No constitutional symptoms were reported · self-categorized by the patient as skin that appeared healthy to them · the lesion involves the back of the hand, arm and leg · close-up view · the patient is a male aged 18–29 · the lesion is described as rough or flaky and raised or bumpy · symptoms reported: itching · the patient reports the condition has been present for about one day: 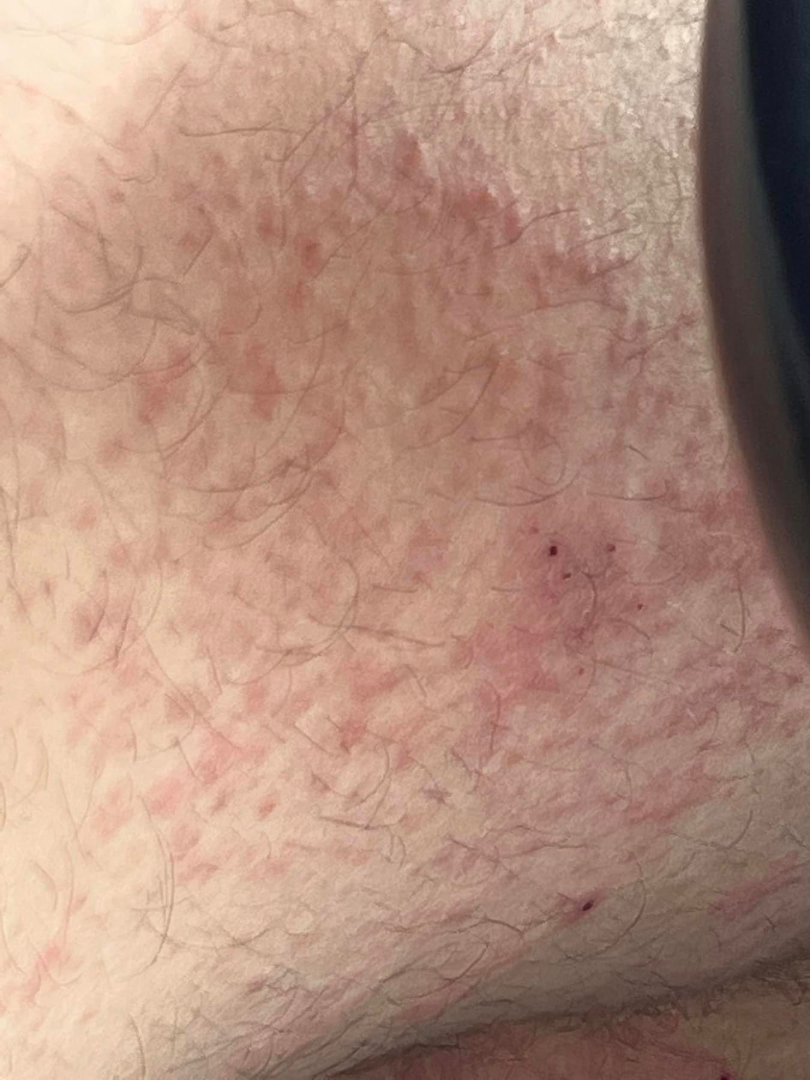  assessment: ungradable on photographic review